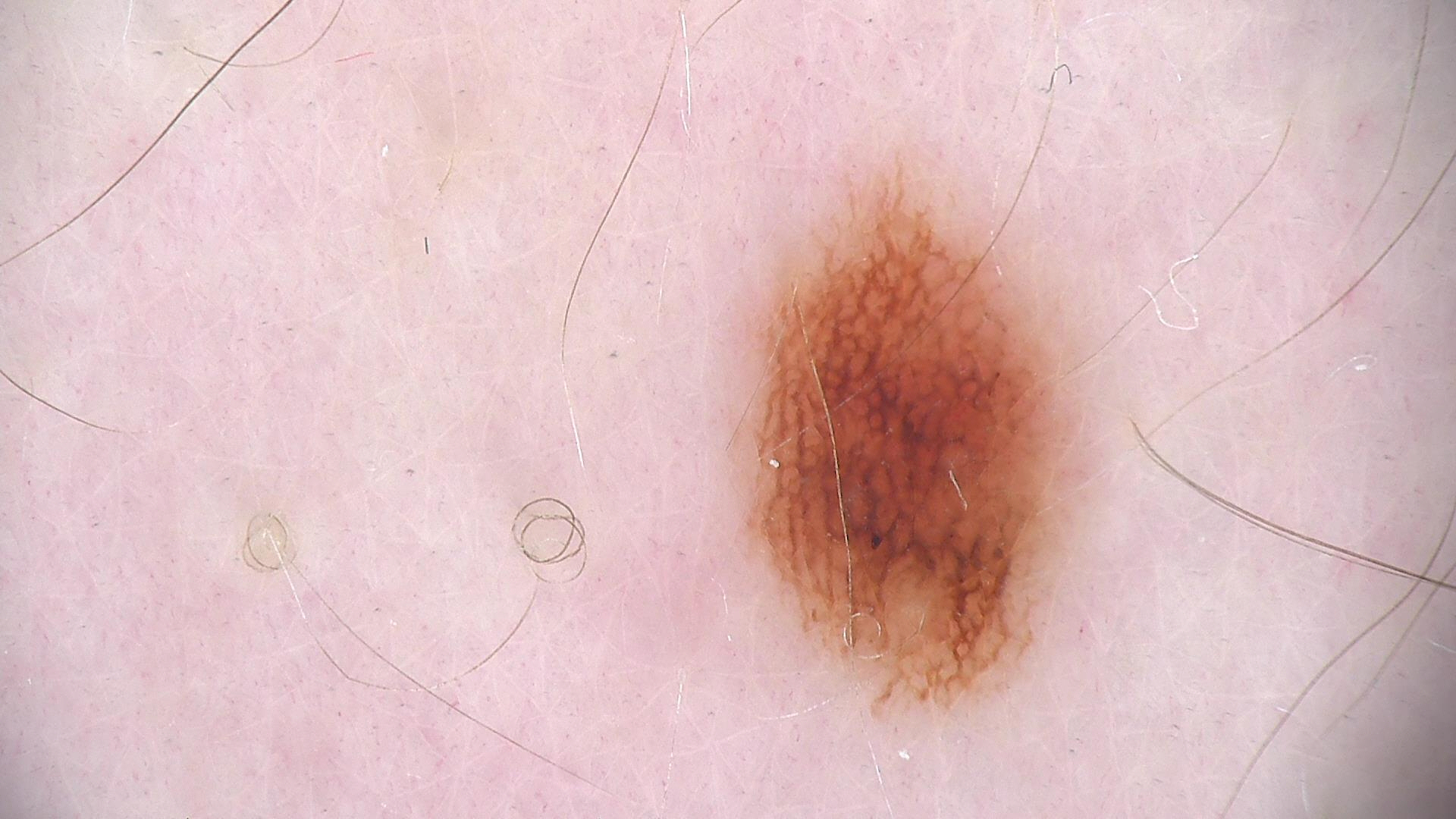Consistent with a dysplastic junctional nevus.